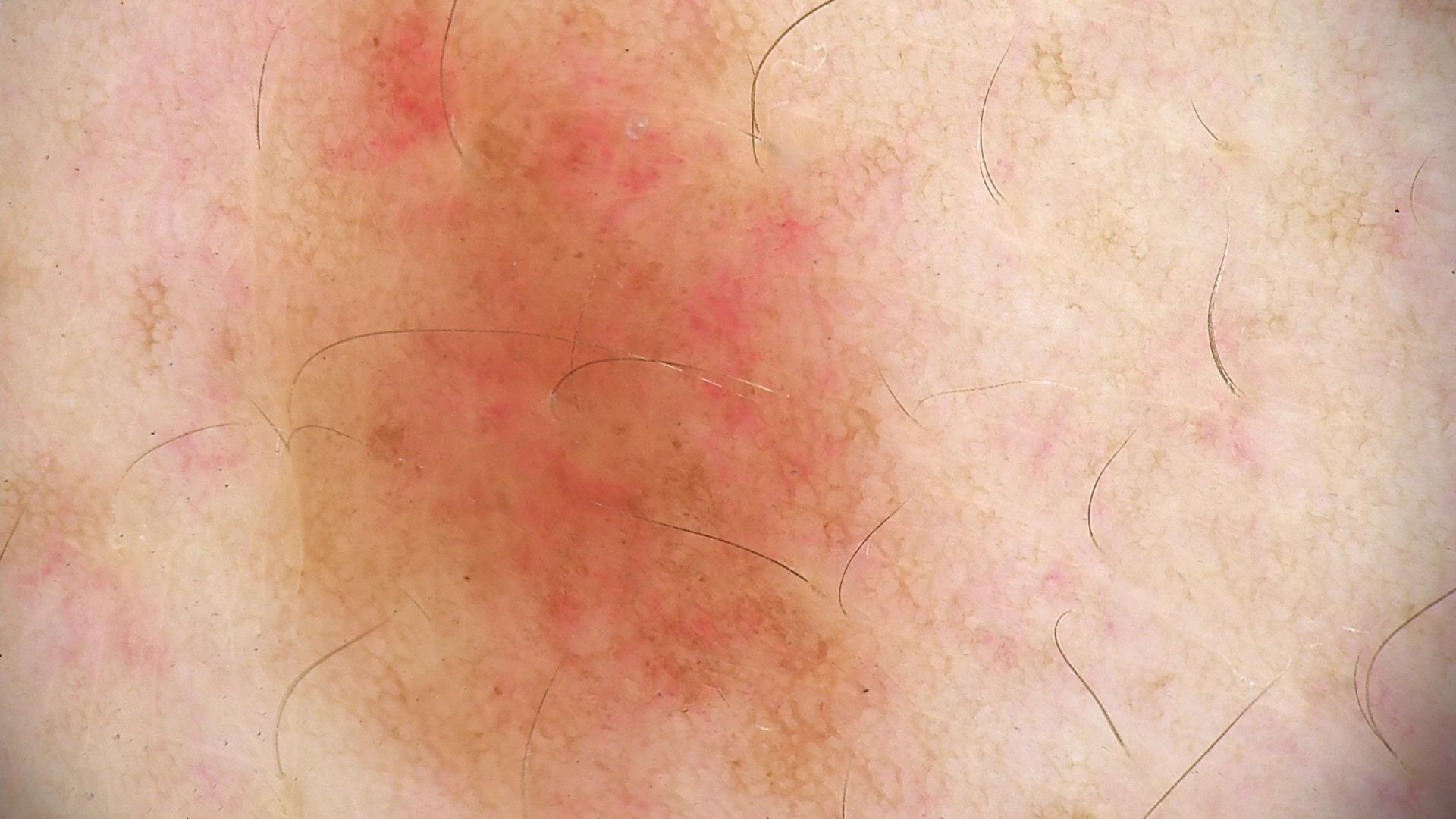A dermatoscopic image of a skin lesion. Labeled as a benign lesion — a dysplastic junctional nevus.